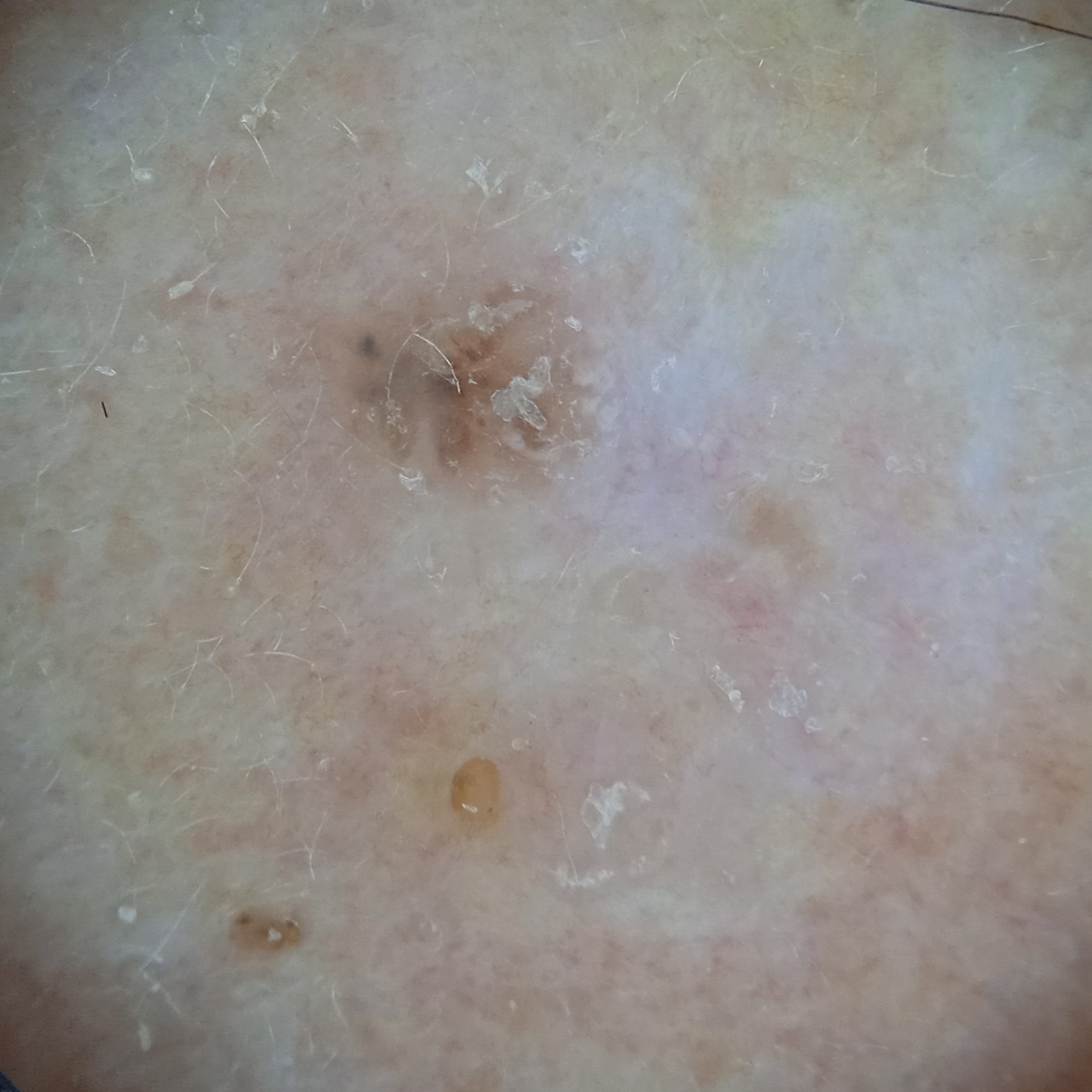imaging: dermatoscopic image; sun reaction: skin tans without first burning; nevus count: few melanocytic nevi overall; anatomic site: the face; size: 6.6 mm; diagnosis: basal cell carcinoma (biopsy-proven).